Dermoscopy of a skin lesion. The patient is a male about 15 years old — 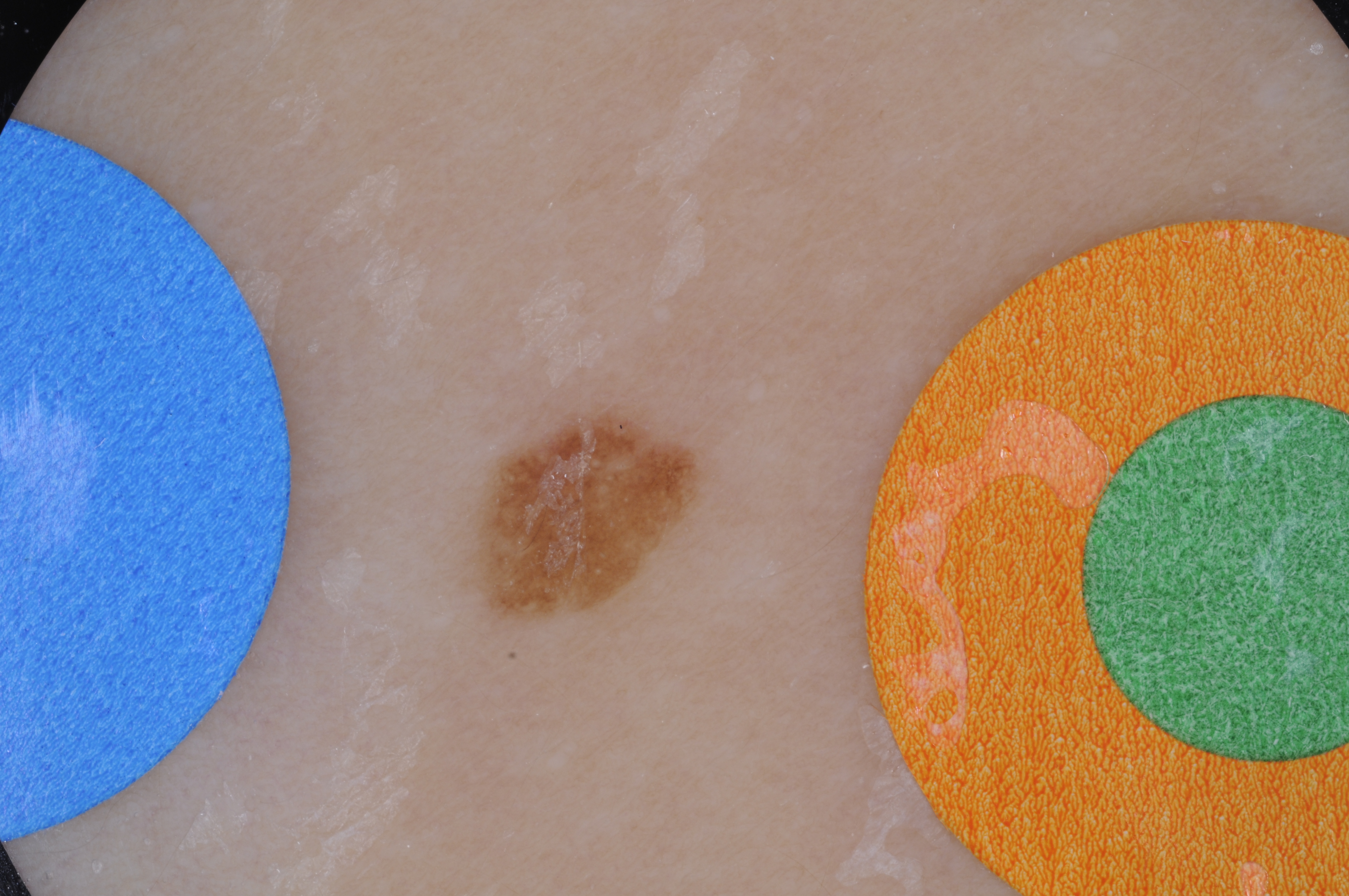The visible lesion spans x1=471 y1=403 x2=707 y2=623.
A small lesion occupying a minor part of the field.
On dermoscopy, the lesion shows milia-like cysts and pigment network.
The lesion was assessed as a melanocytic nevus.